The arm is involved. This image was taken at an angle: 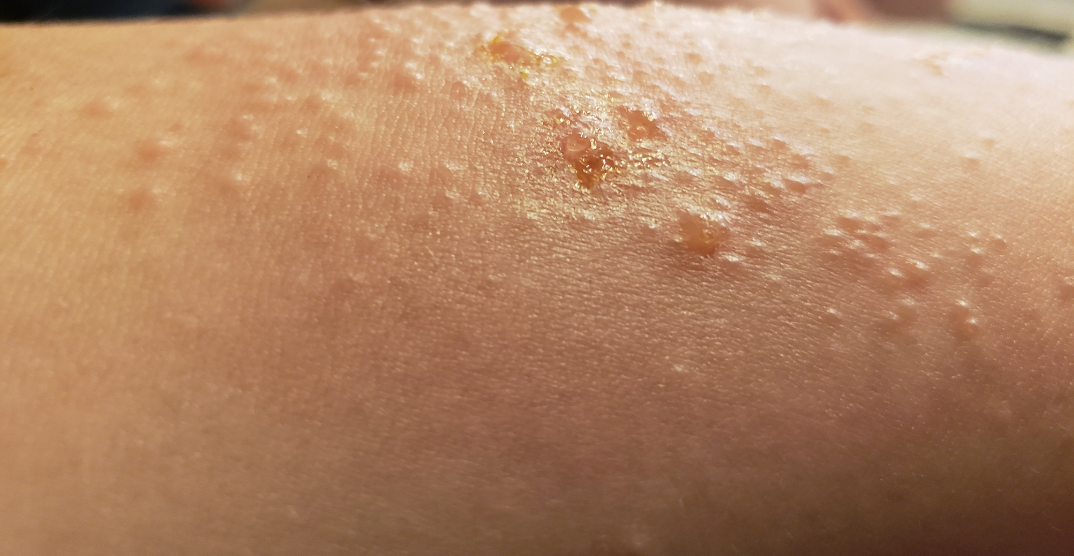differential:
  leading:
    - Allergic Contact Dermatitis
  considered:
    - Impetigo